The lesion involves the leg; reported lesion symptoms include itching; this is a close-up image: 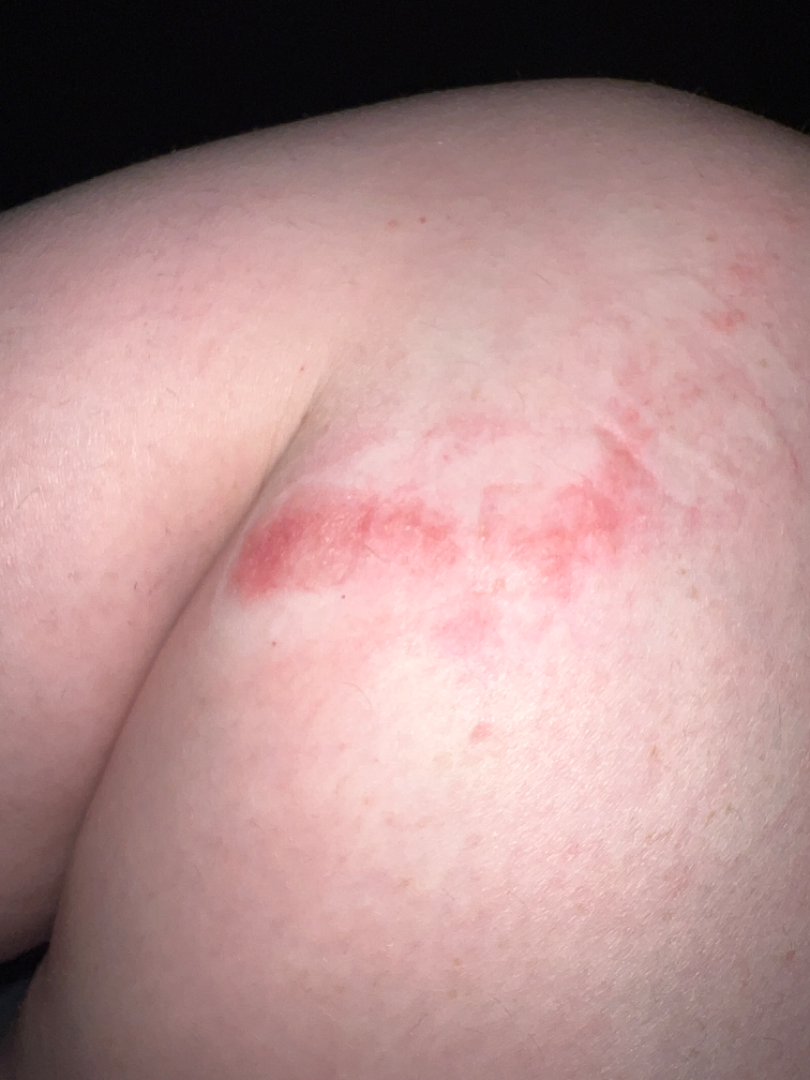differential diagnosis=the reviewer's impression was Allergic Contact Dermatitis.